The photograph is a close-up of the affected area.
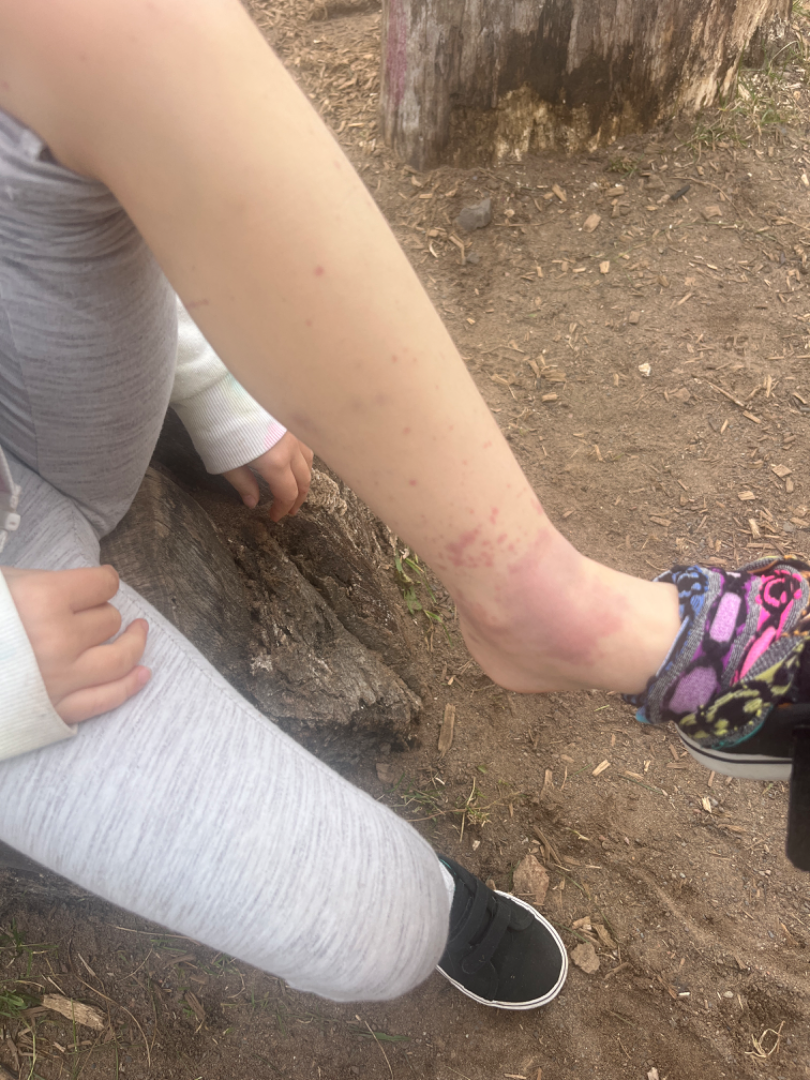| key | value |
|---|---|
| differential diagnosis | favoring Leukocytoclastic Vasculitis; with consideration of Irritant Contact Dermatitis |